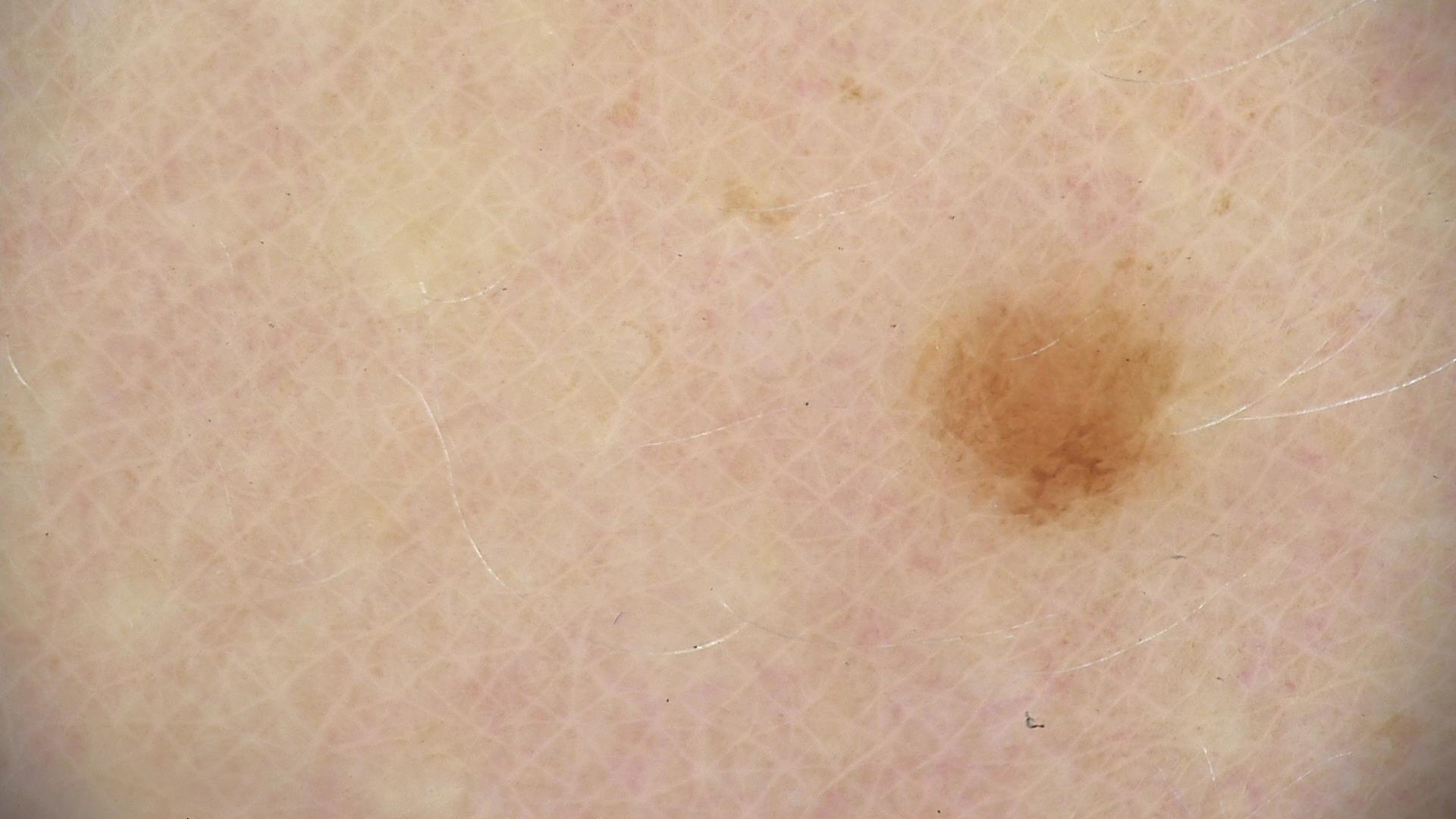A dermoscopy image of a single skin lesion. The diagnostic label was a dysplastic junctional nevus.